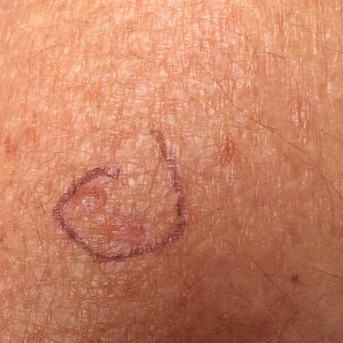image: clinical photograph
patient:
  age: 41
symptoms:
  present:
    - itching
diagnosis:
  name: actinic keratosis
  code: ACK
  malignancy: indeterminate
  confirmation: clinical consensus